A clinical photograph of a skin lesion. Collected as part of a research study, without a referral diagnosis. A male patient aged 73: 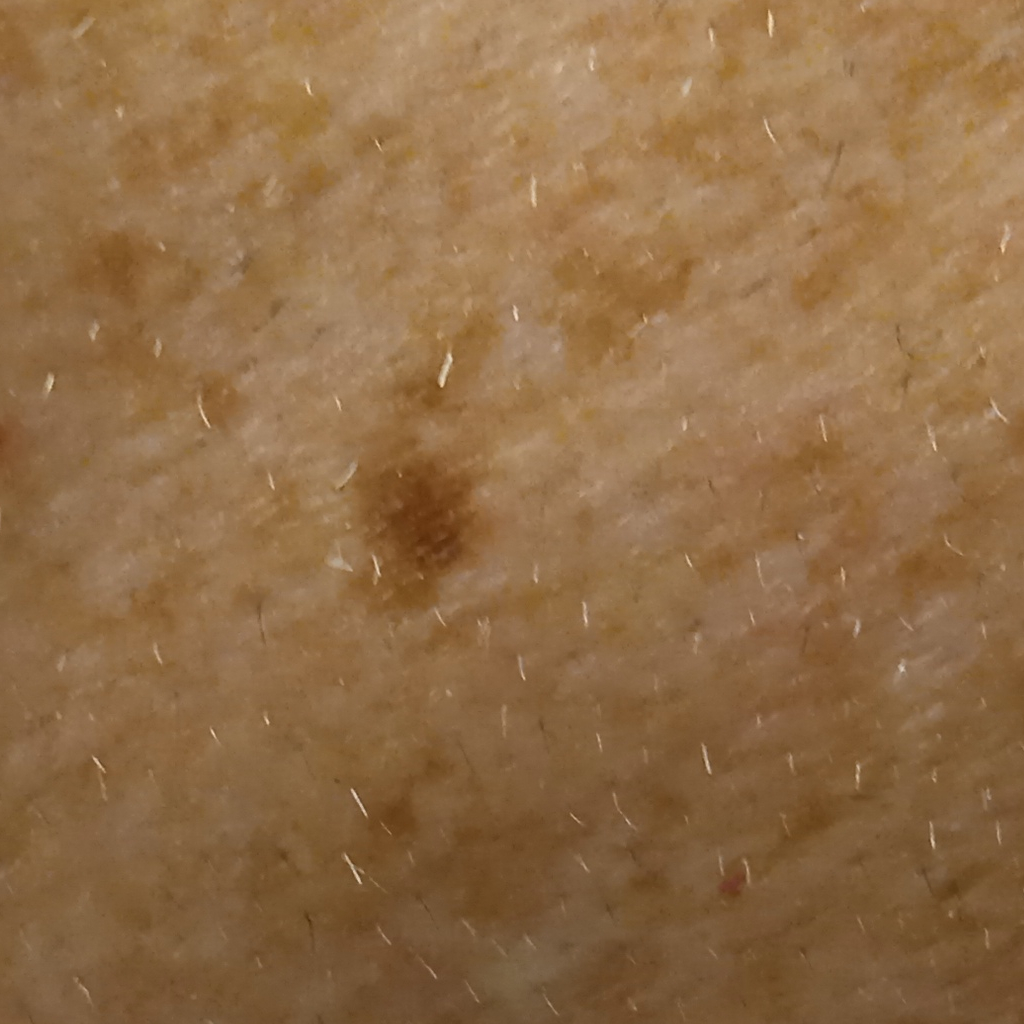Case summary:
The lesion is on the torso.
Assessment:
The diagnostic impression was a melanoma.